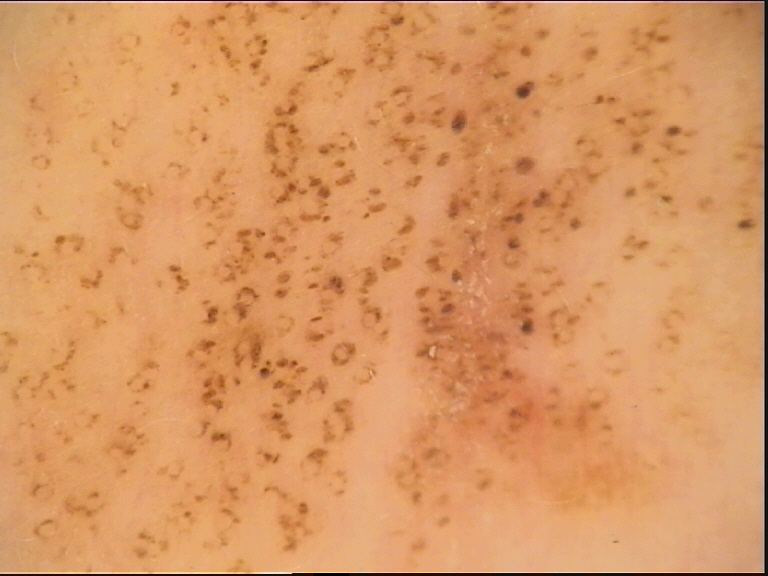Summary:
A dermoscopic image of a skin lesion.
Impression:
Classified as a benign lesion — a dysplastic junctional nevus.